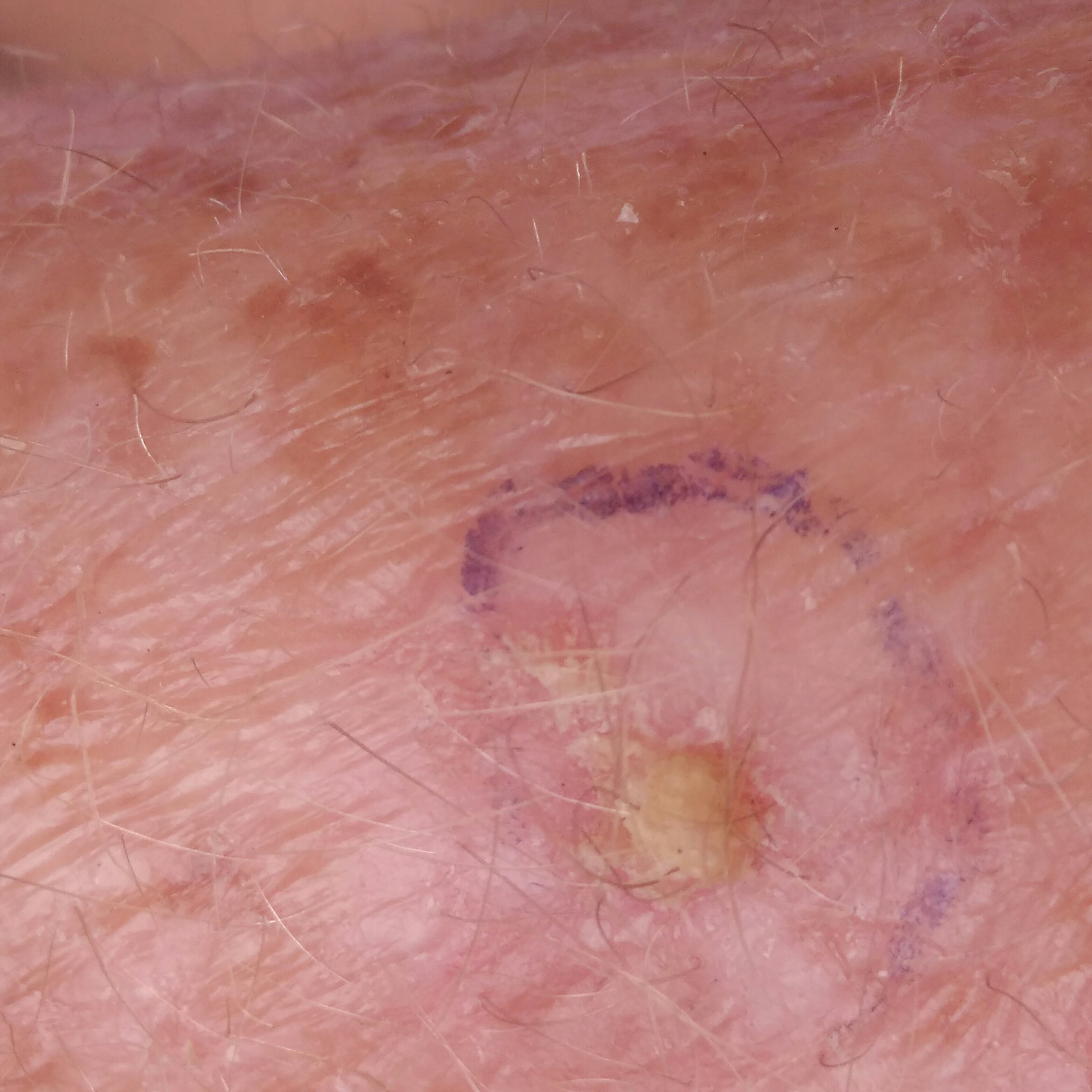A clinical close-up photograph of a skin lesion. By the patient's account, the lesion is elevated and itches, but does not hurt and has not bled. Consistent with an actinic keratosis.